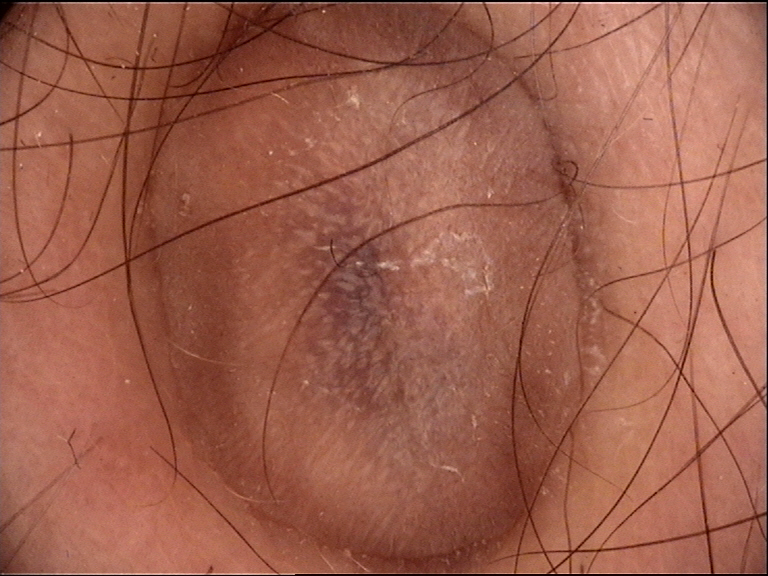Diagnosed as a benign lesion — a dermatofibroma.